This image was taken at a distance — 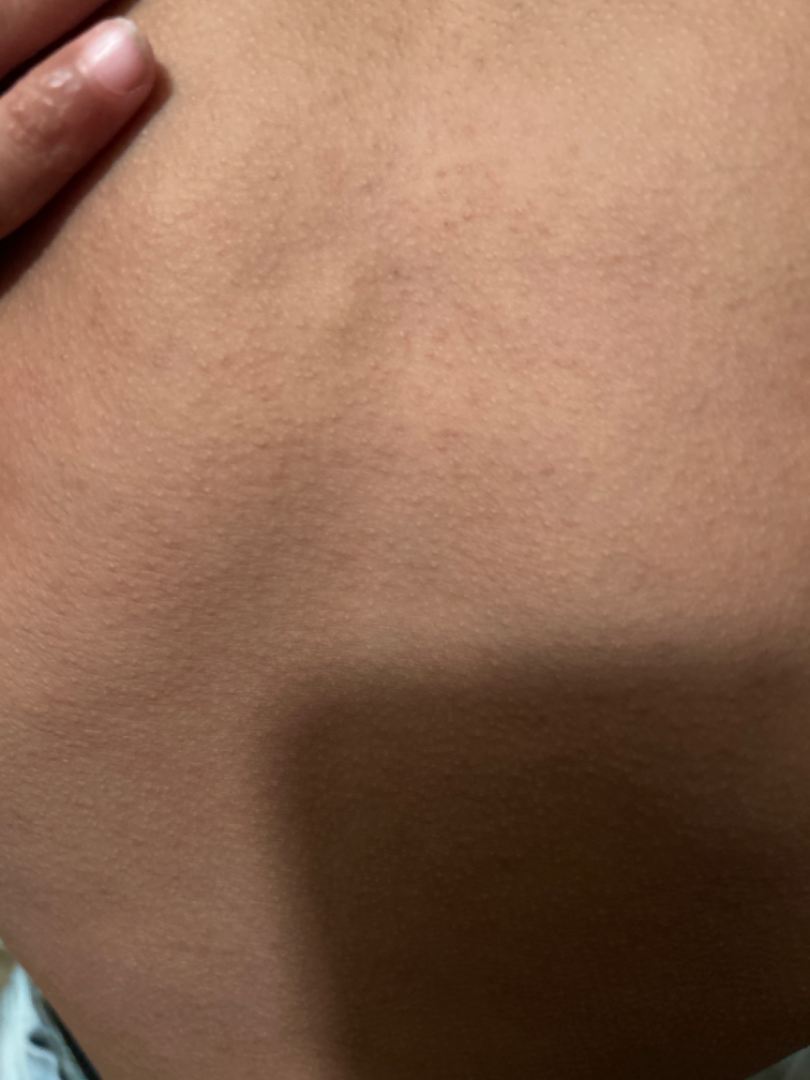Impression: Single-reviewer assessment: the differential is split between Keratosis pilaris and Eczema.